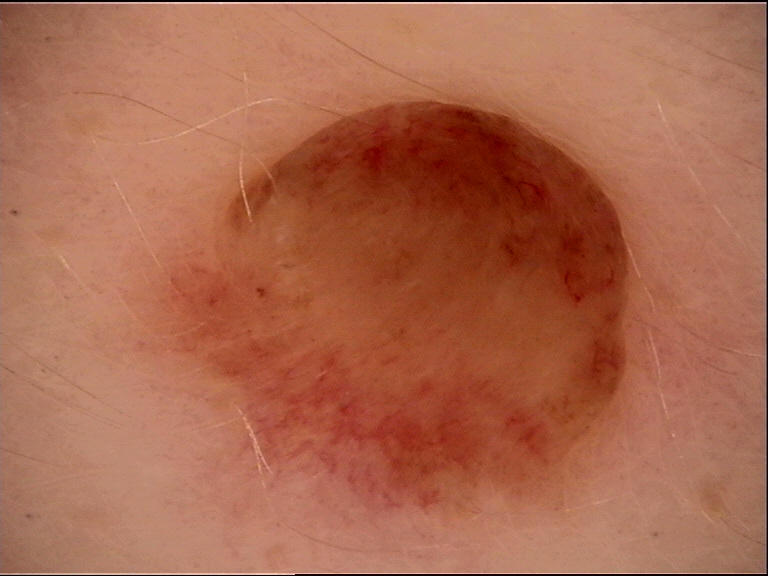modality: dermoscopy
assessment: dermal nevus (expert consensus)